A skin lesion imaged with a dermatoscope.
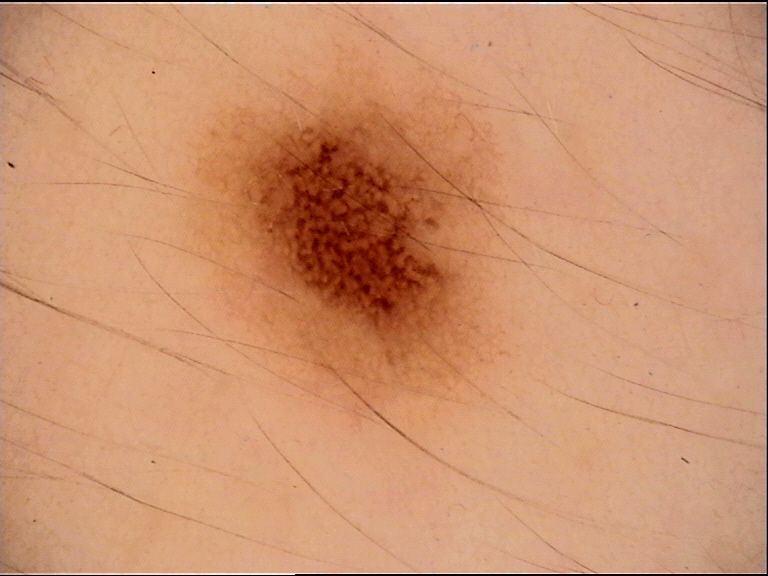{
  "diagnosis": {
    "name": "dysplastic junctional nevus",
    "code": "jd",
    "malignancy": "benign",
    "super_class": "melanocytic",
    "confirmation": "expert consensus"
  }
}